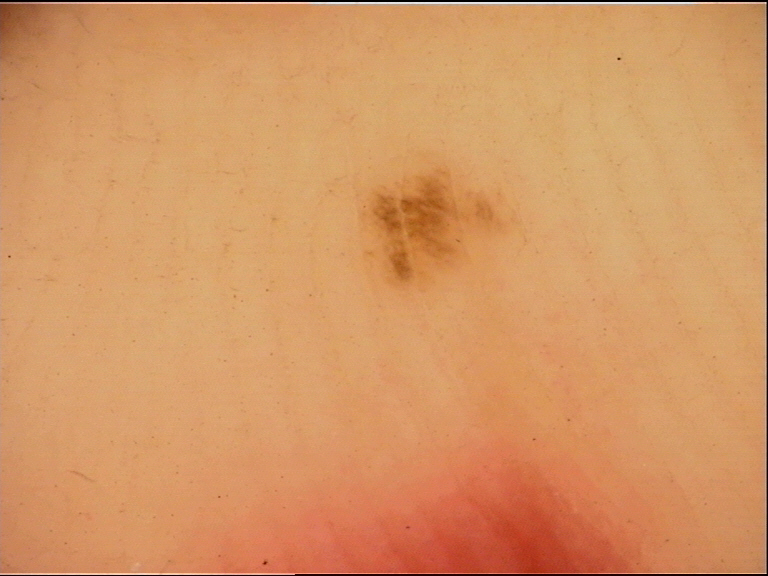imaging — dermatoscopy | lesion type — banal | label — acral junctional nevus (expert consensus).